A dermoscopic close-up of a skin lesion.
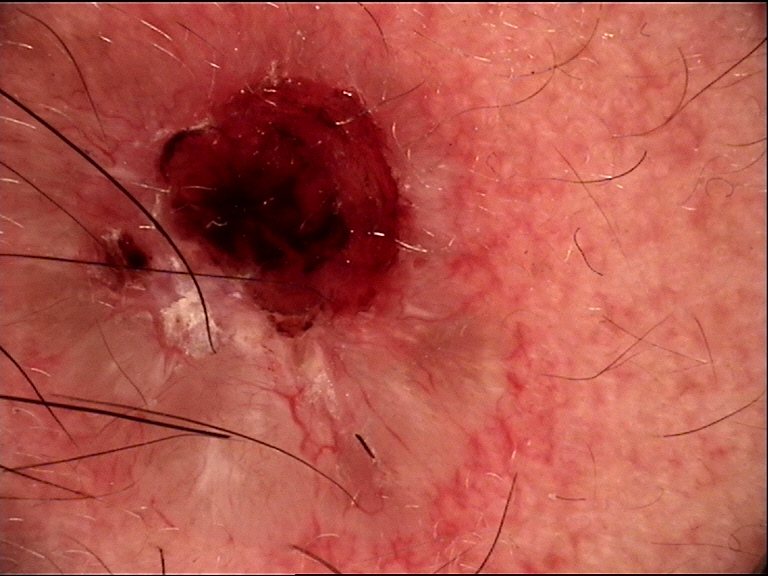This is a keratinocytic lesion.
Histopathologically confirmed as a skin cancer — a basal cell carcinoma.